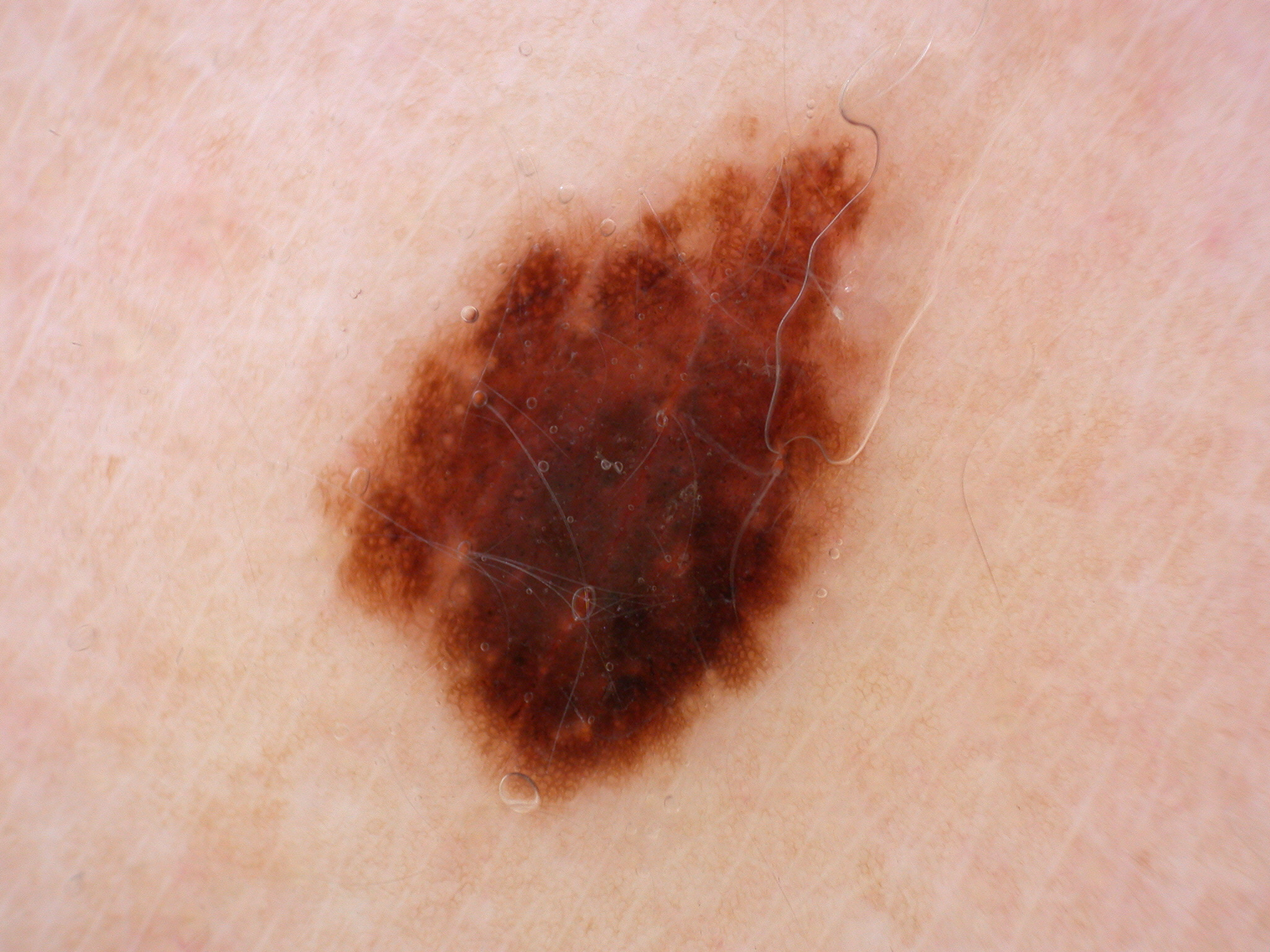Q: How was this image acquired?
A: dermatoscopic image of a skin lesion
Q: Where is the lesion located?
A: [319,108,914,820]
Q: What did the assessment conclude?
A: a melanocytic nevus